A dermoscopic image of a skin lesion:
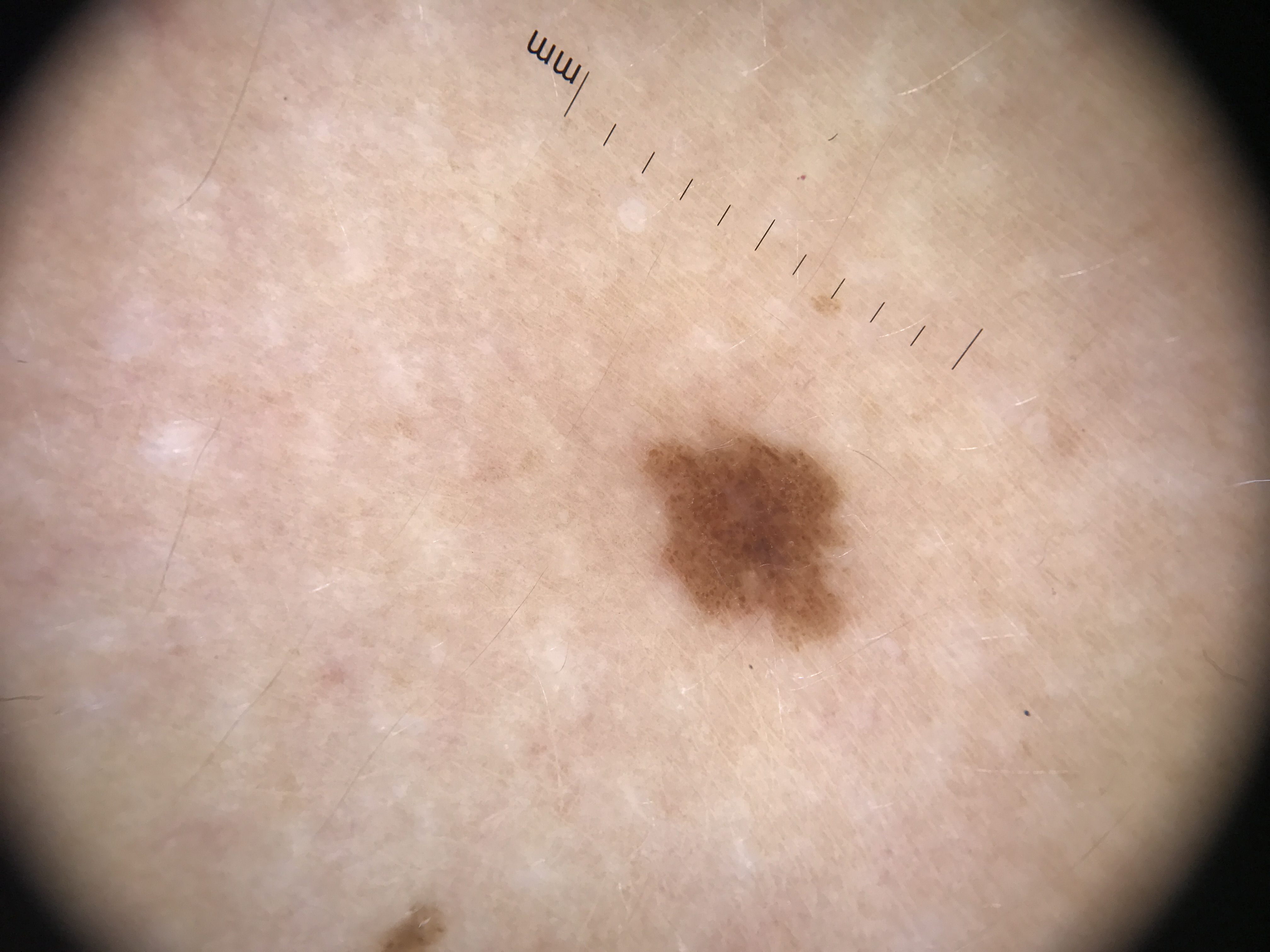assessment: dysplastic junctional nevus (expert consensus).